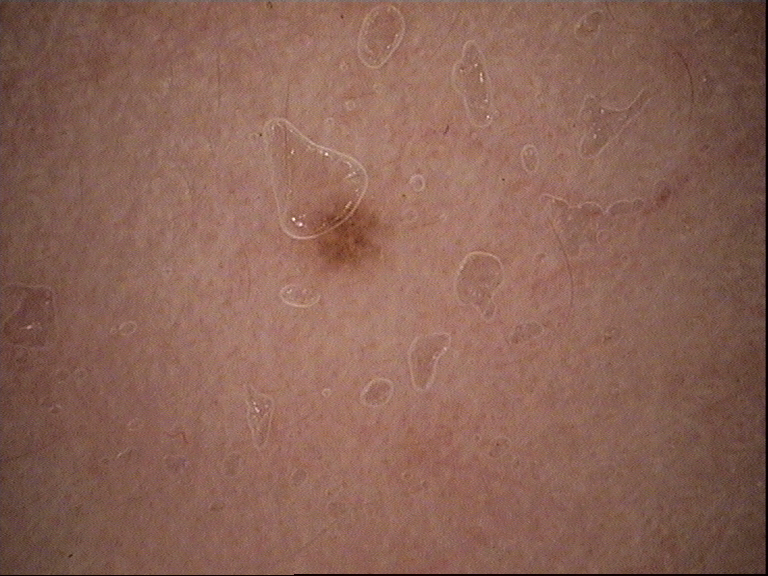Impression:
Classified as a dysplastic junctional nevus.